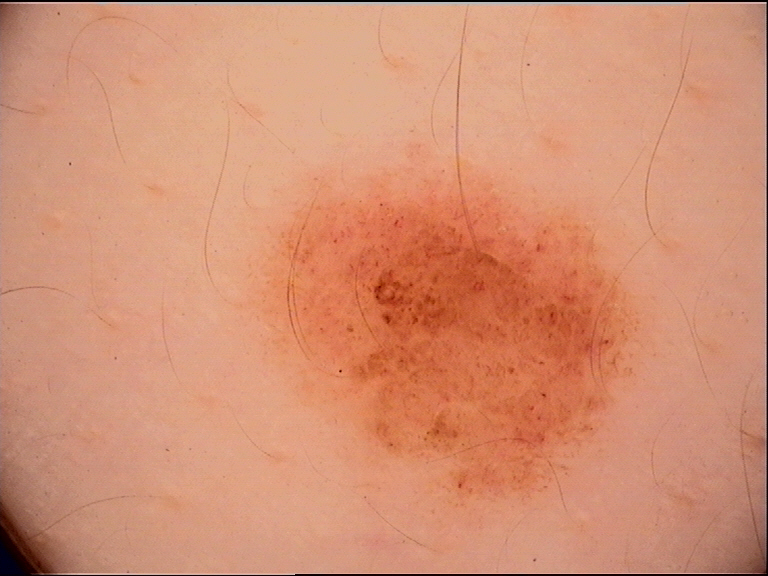The diagnostic label was a compound nevus.